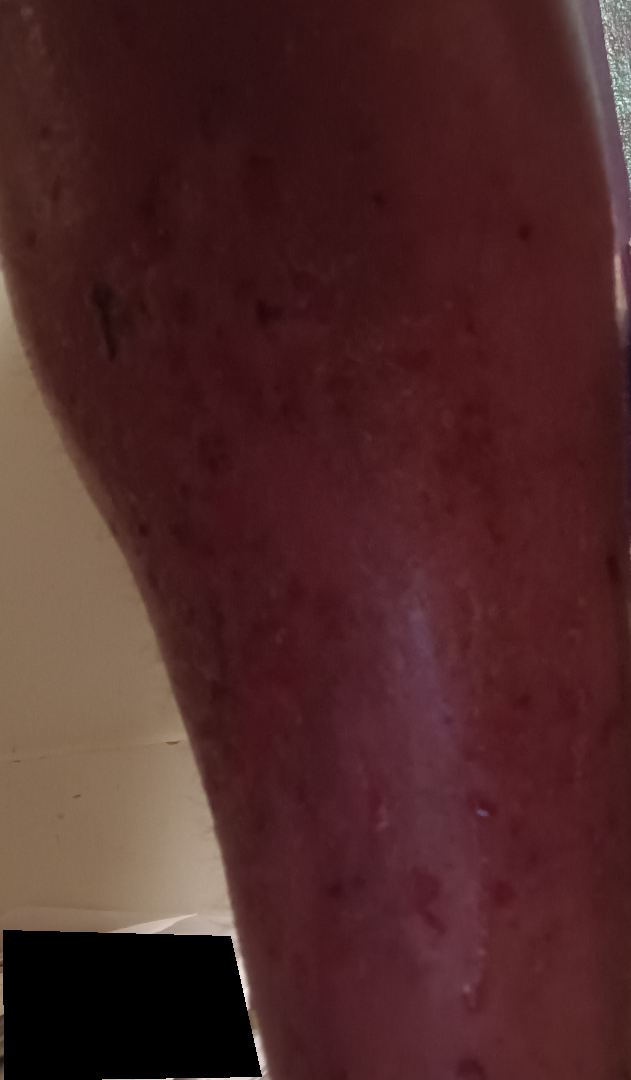Notes:
– photo taken: close-up
– texture: rough or flaky, fluid-filled and raised or bumpy
– patient describes the issue as: a rash
– subject: female
– site: leg
– skin tone: Fitzpatrick phototype V
– present for: one to three months
– other reported symptoms: joint pain and chills
– diagnostic considerations: most consistent with Stasis Dermatitis; also raised was Cellulitis; also on the differential is Eczema